By self-report, no sunbed use and no immunosuppression; a female patient age 81; a dermoscopy image of a skin lesion; the patient says their skin reddens painfully with sun exposure; collected as part of a research study, without a referral diagnosis; the patient describes having a moderate number of moles — 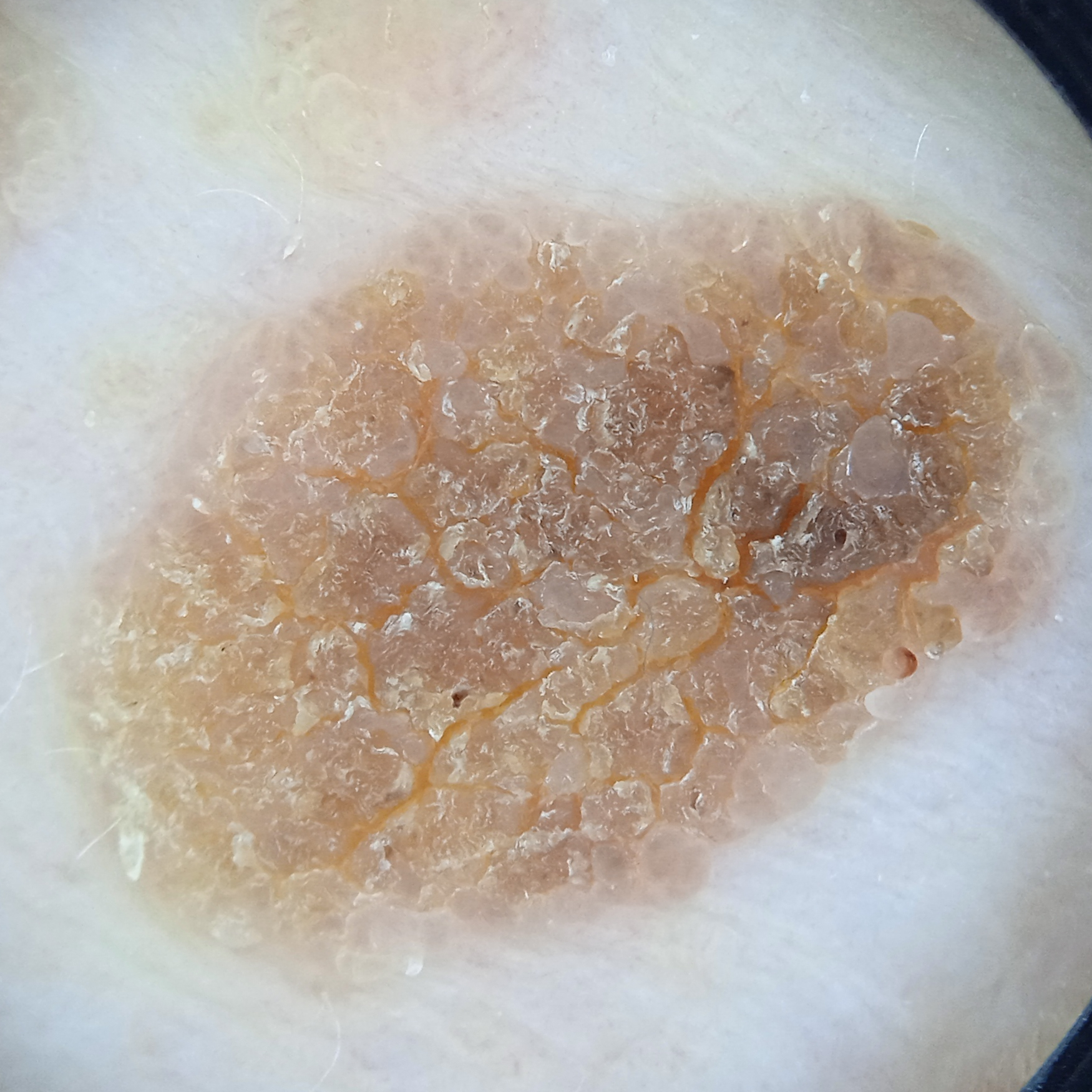{"lesion_size": {"diameter_mm": 12.2}, "diagnosis": {"name": "seborrheic keratosis", "malignancy": "benign"}}